The lesion involves the leg, back of the hand, palm, head or neck, sole of the foot and arm; close-up view — 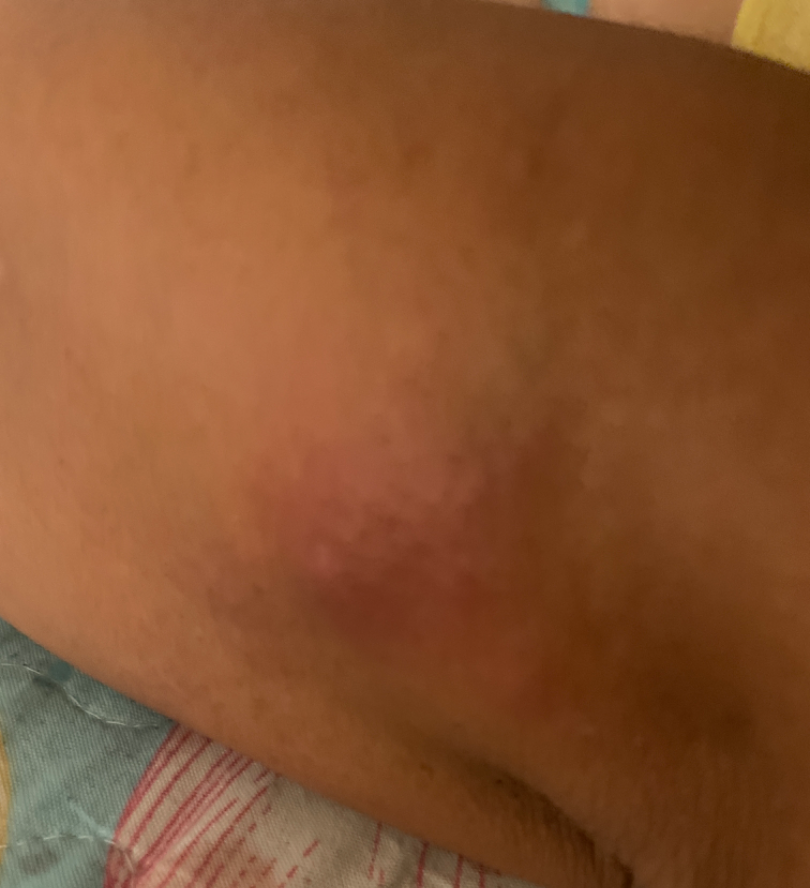assessment: not assessable